Located on the top or side of the foot and leg. This image was taken at a distance. The contributor is 70–79, female.
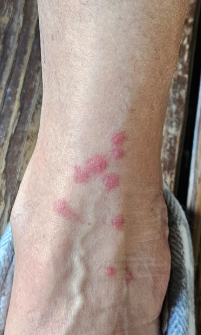No constitutional symptoms were reported. The contributor reports itching and bothersome appearance. The condition has been present for less than one week. The contributor reports the lesion is raised or bumpy and flat. The differential is split between Insect Bite and Dermatosis due to flea.